Close-up view · located on the back of the torso, arm, back of the hand, front of the torso, leg, head or neck and top or side of the foot · the patient reports the condition has been present for more than one year · the patient reports pain, bleeding, itching, enlargement, bothersome appearance and darkening · Fitzpatrick III; lay graders estimated 3 on the Monk skin tone scale · the lesion is described as fluid-filled, flat, raised or bumpy and rough or flaky.
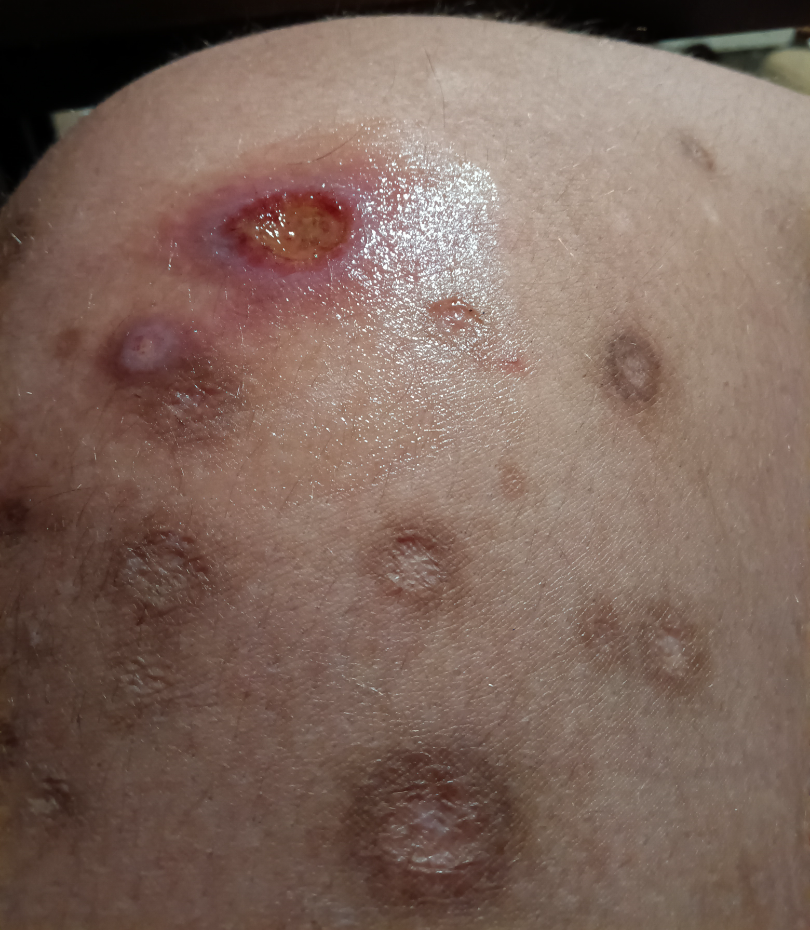On photographic review by a dermatologist, Skin lesion in drug addict (favored); Ecthyma (considered); Acute ulcer of skin (lower probability).